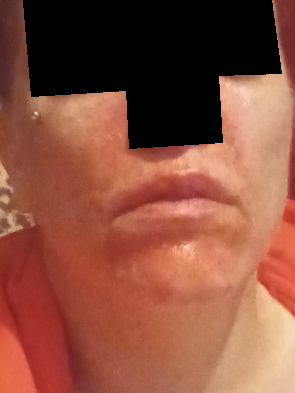Findings:
The condition could not be reliably identified from the image.
Background:
This image was taken at a distance. Present for less than one week. Located on the head or neck. The contributor reports darkening, bothersome appearance, pain and burning. The patient described the issue as a rash. No relevant systemic symptoms. Female patient, age 40–49.